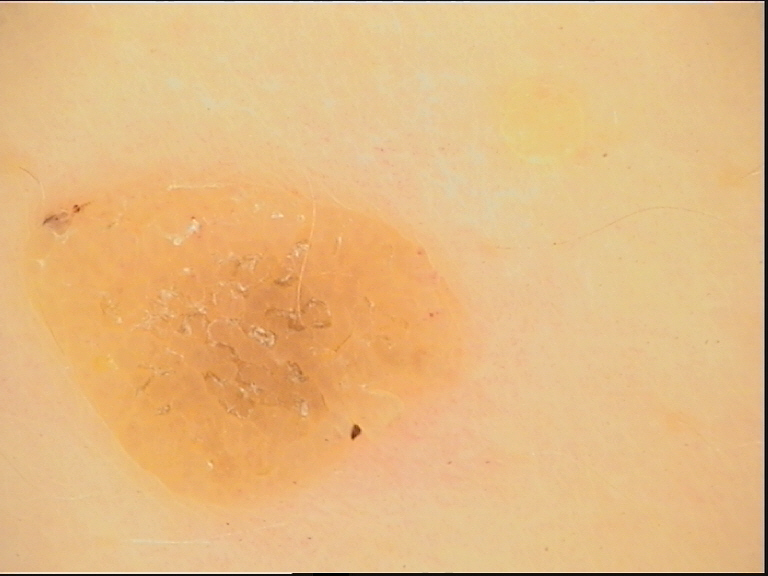Impression: Diagnosed as a seborrheic keratosis.